The contributor is 50–59, female. A close-up photograph. The lesion involves the front of the torso.
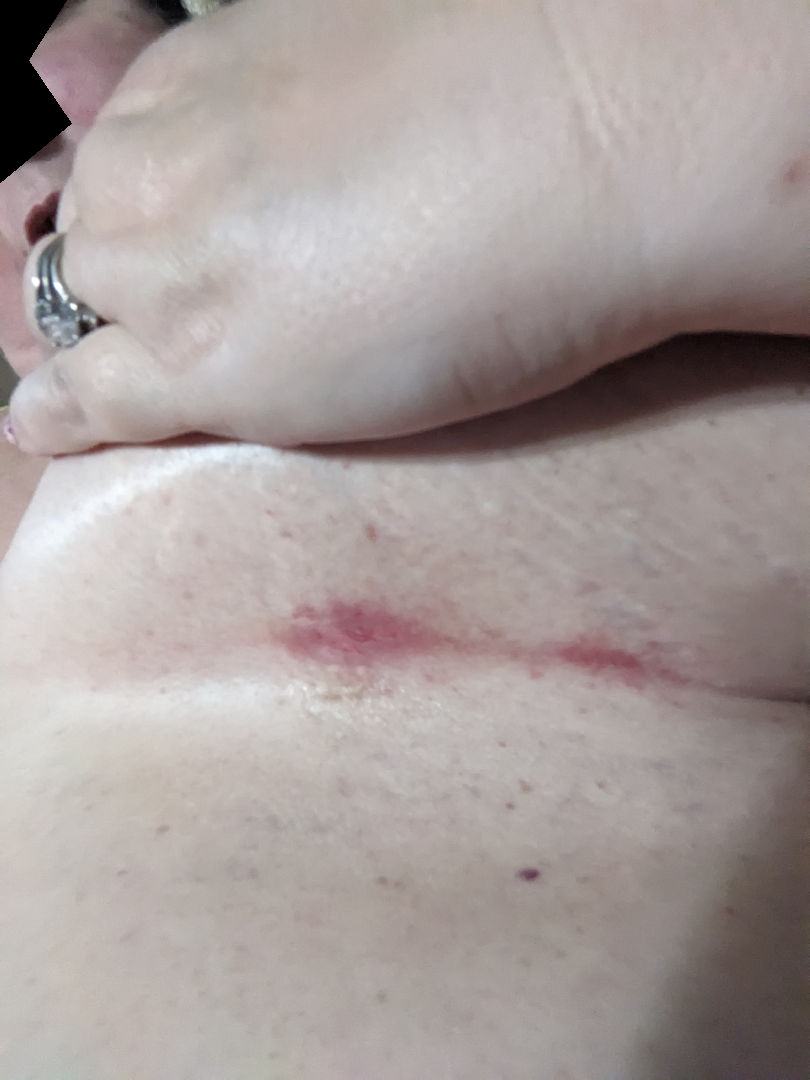texture: raised or bumpy
present for: one to four weeks
symptoms: itching
patient's own categorization: a rash
diagnostic considerations: the leading impression is Intertrigo; the differential also includes skin fissure; less probable is Hailey Hailey disease